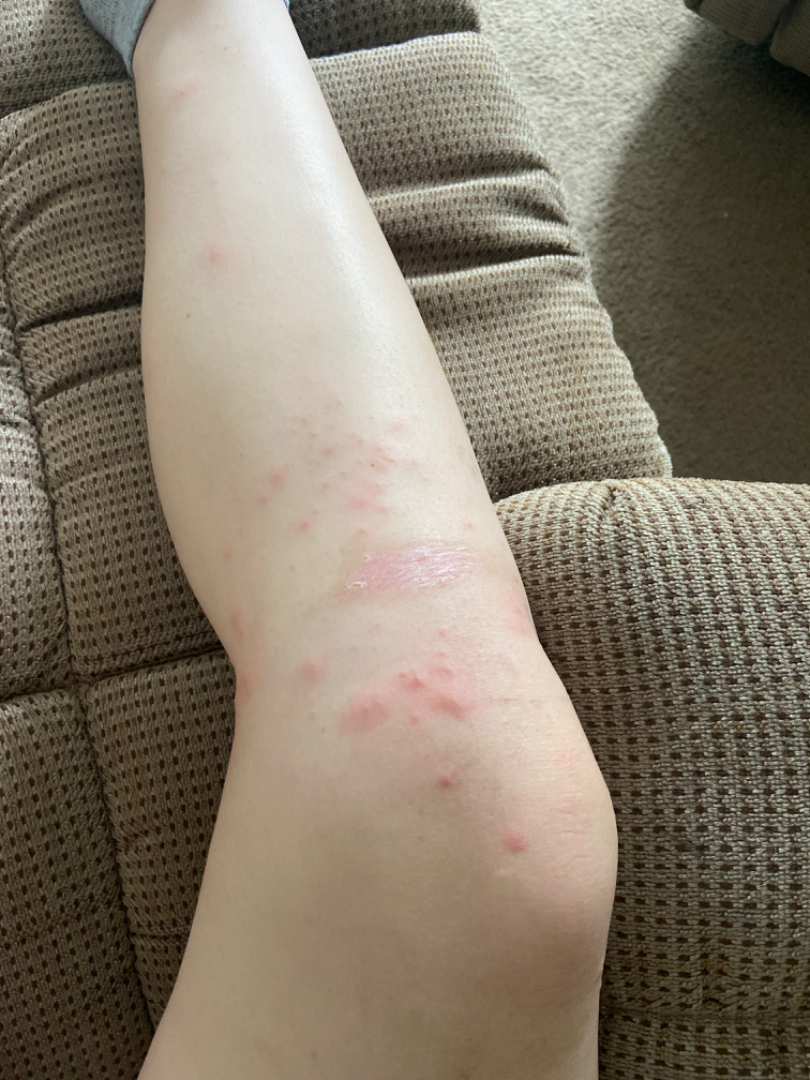Female contributor, age 18–29. Self-categorized by the patient as a rash. No relevant systemic symptoms. The photograph was taken at a distance. Skin tone: FST III; lay reviewers estimated MST 1 (US pool) or 2 (India pool). Reported duration is one to four weeks. The lesion is associated with itching and bothersome appearance. Located on the leg. Texture is reported as fluid-filled and raised or bumpy. A single dermatologist reviewed the case: in keeping with Folliculitis.